Female contributor, age 50–59. The photograph was taken at an angle. Present for more than one year. The patient reports burning, enlargement, itching, bleeding and pain. Located on the palm, back of the hand and arm. The patient described the issue as a rash. The lesion is described as rough or flaky, raised or bumpy and fluid-filled: 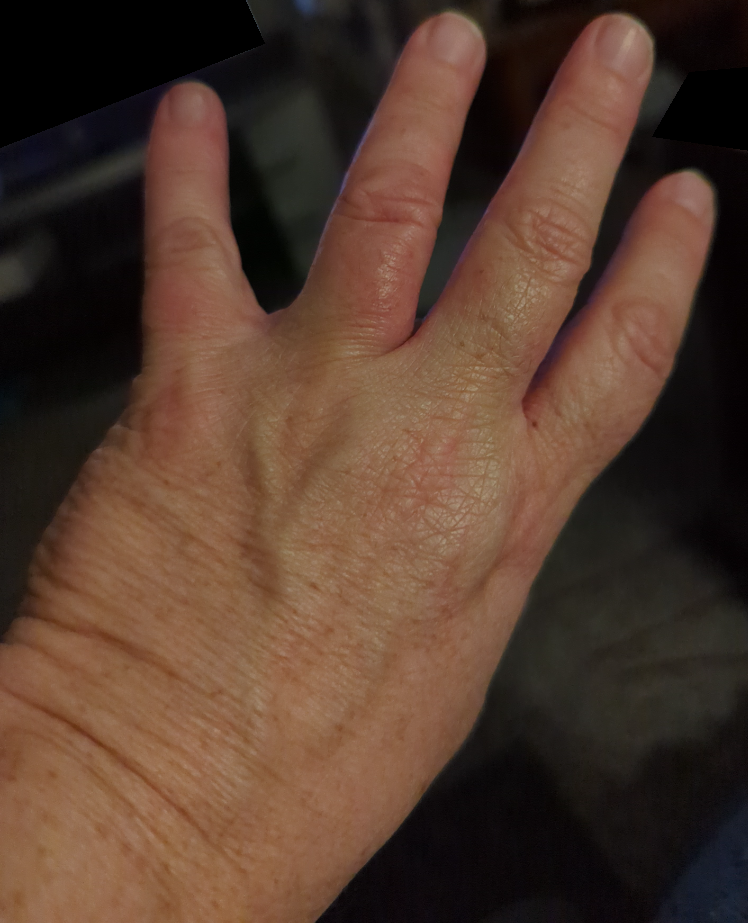Assessment:
On photographic review: most consistent with Eczema.